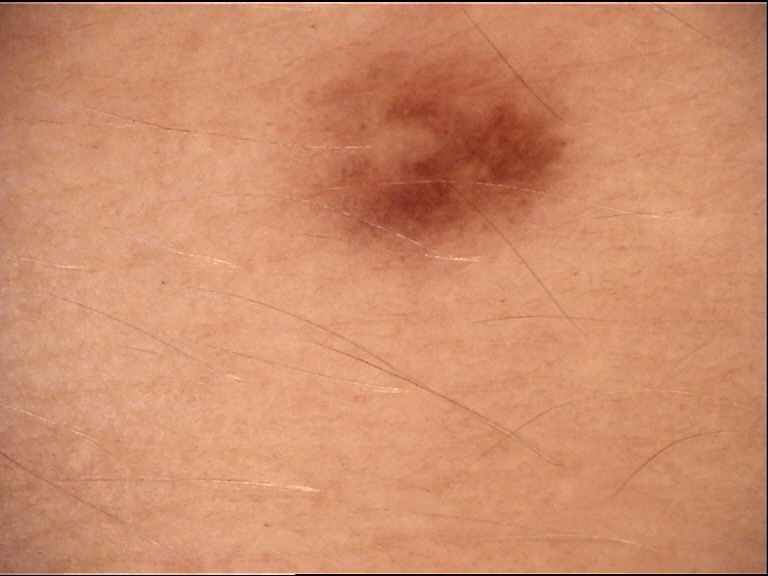Conclusion:
Classified as a dysplastic junctional nevus.